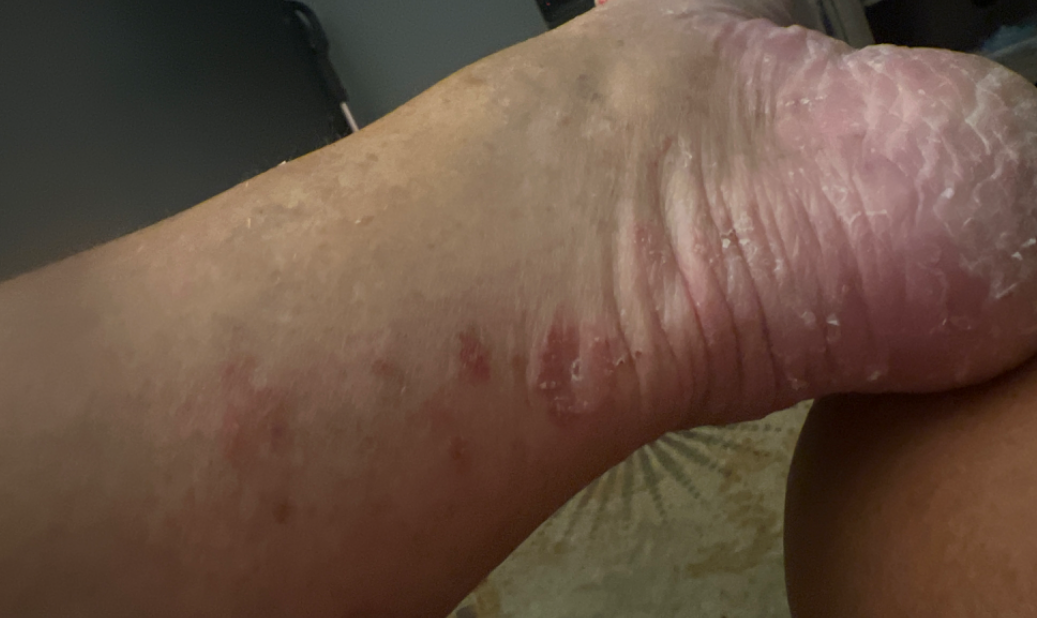{
  "assessment": "indeterminate",
  "shot_type": "close-up",
  "symptoms": "itching",
  "patient_category": "a rash",
  "body_site": "leg"
}